A dermoscopic image of a skin lesion · a male patient about 55 years old — 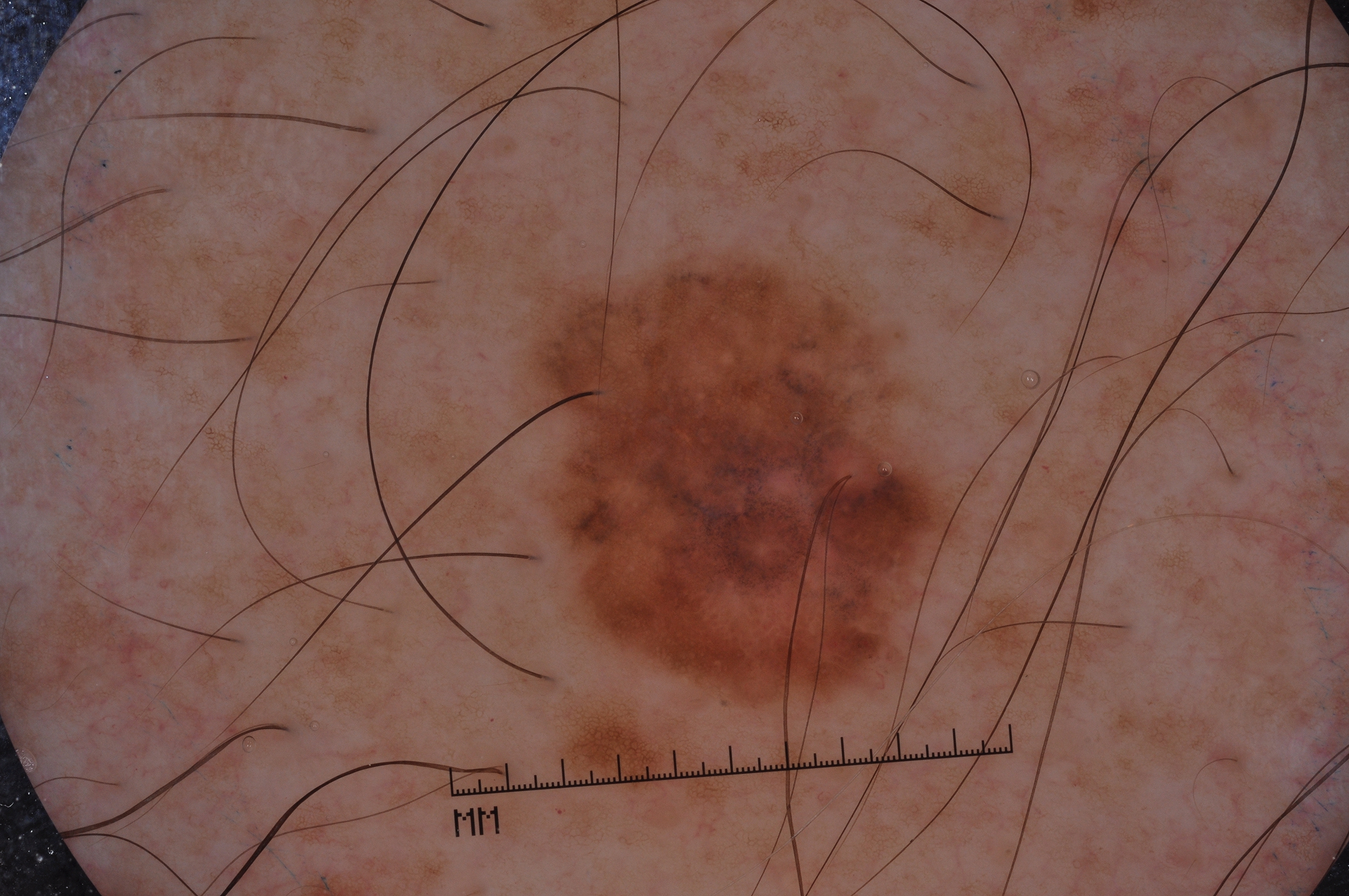dermoscopic findings=pigment network and negative network; absent: milia-like cysts and streaks
location=(527, 259, 948, 700)
diagnostic label=a melanoma